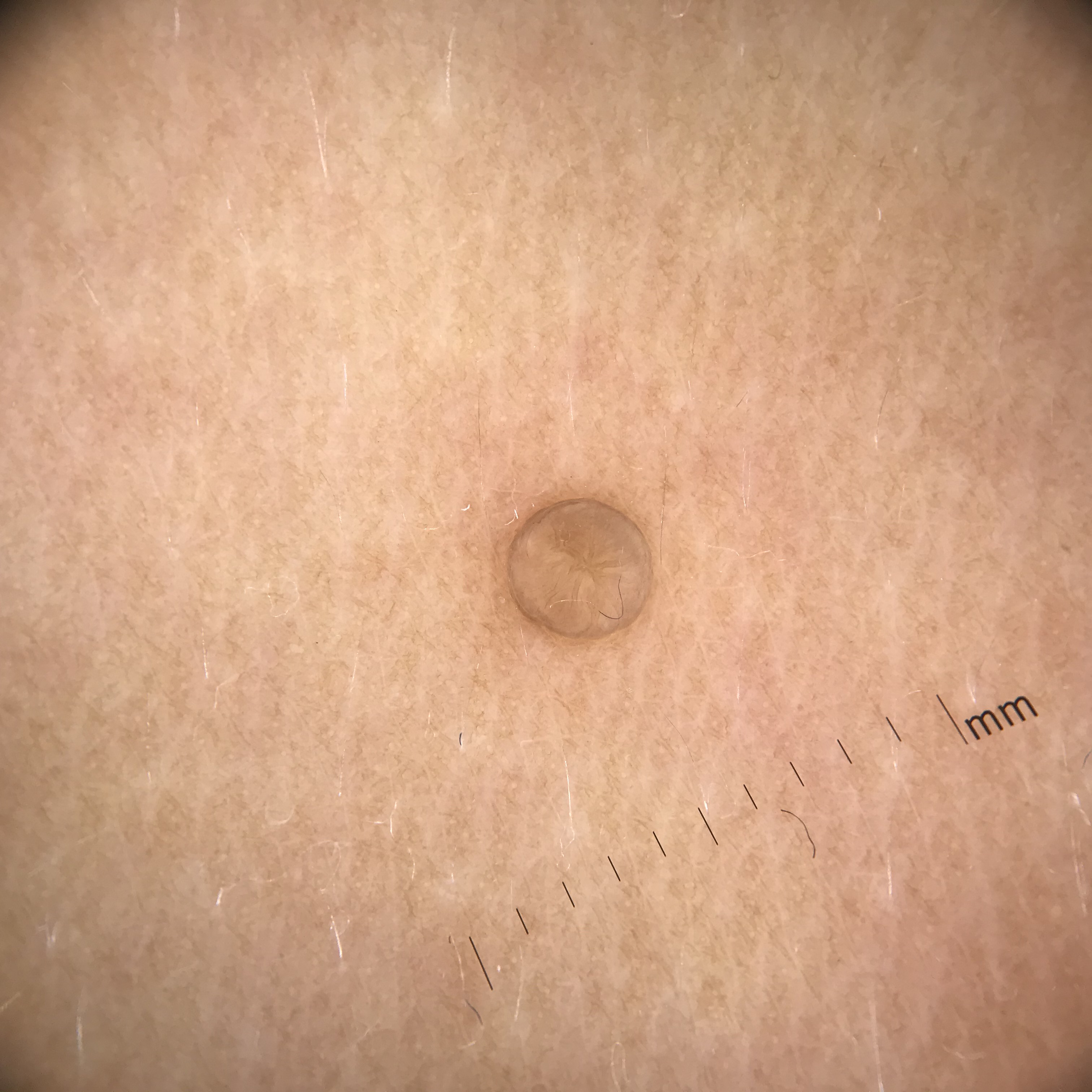* image · dermatoscopy
* category · banal
* diagnosis · dermal nevus (expert consensus)